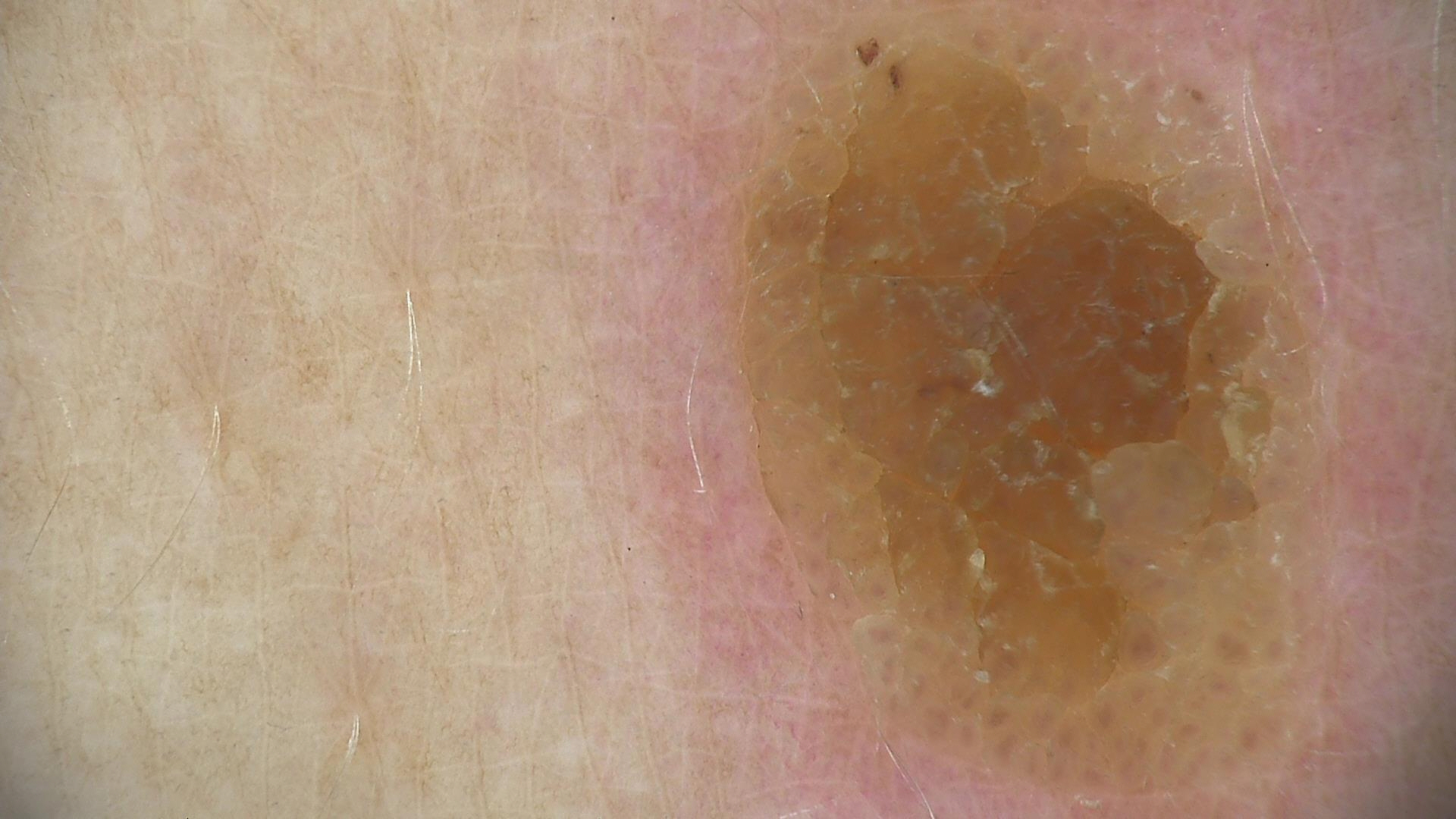Diagnosed as a seborrheic keratosis.